Present for one to four weeks, the photo was captured at an angle, the back of the hand is involved, the contributor is a male aged 18–29, the lesion is associated with itching, the patient described the issue as a rash, no constitutional symptoms were reported, the lesion is described as raised or bumpy and rough or flaky — 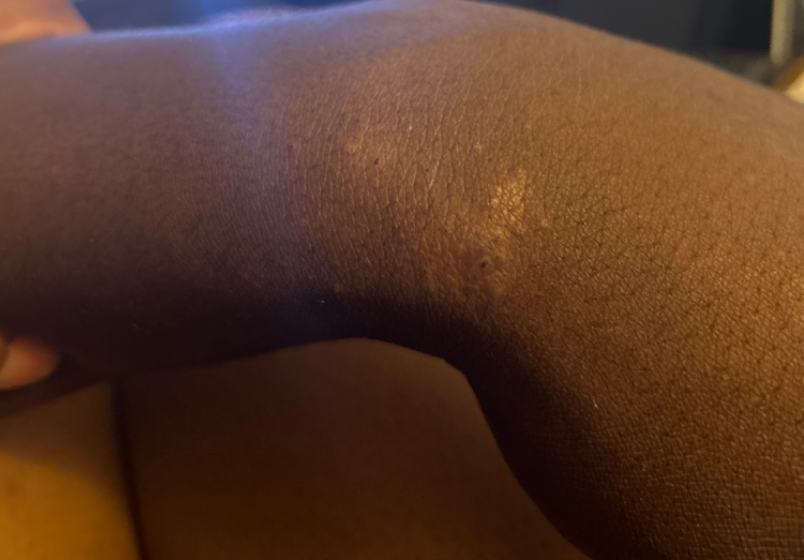| key | value |
|---|---|
| differential | Eczema (weight 0.78); Psoriasis (weight 0.11); Lichen planus/lichenoid eruption (weight 0.11) |